Acquired for a research image collection, with no referral diagnosis. Dermoscopy of a skin lesion. The patient says their skin tans without first burning. Few moles overall by the patient's own estimate — 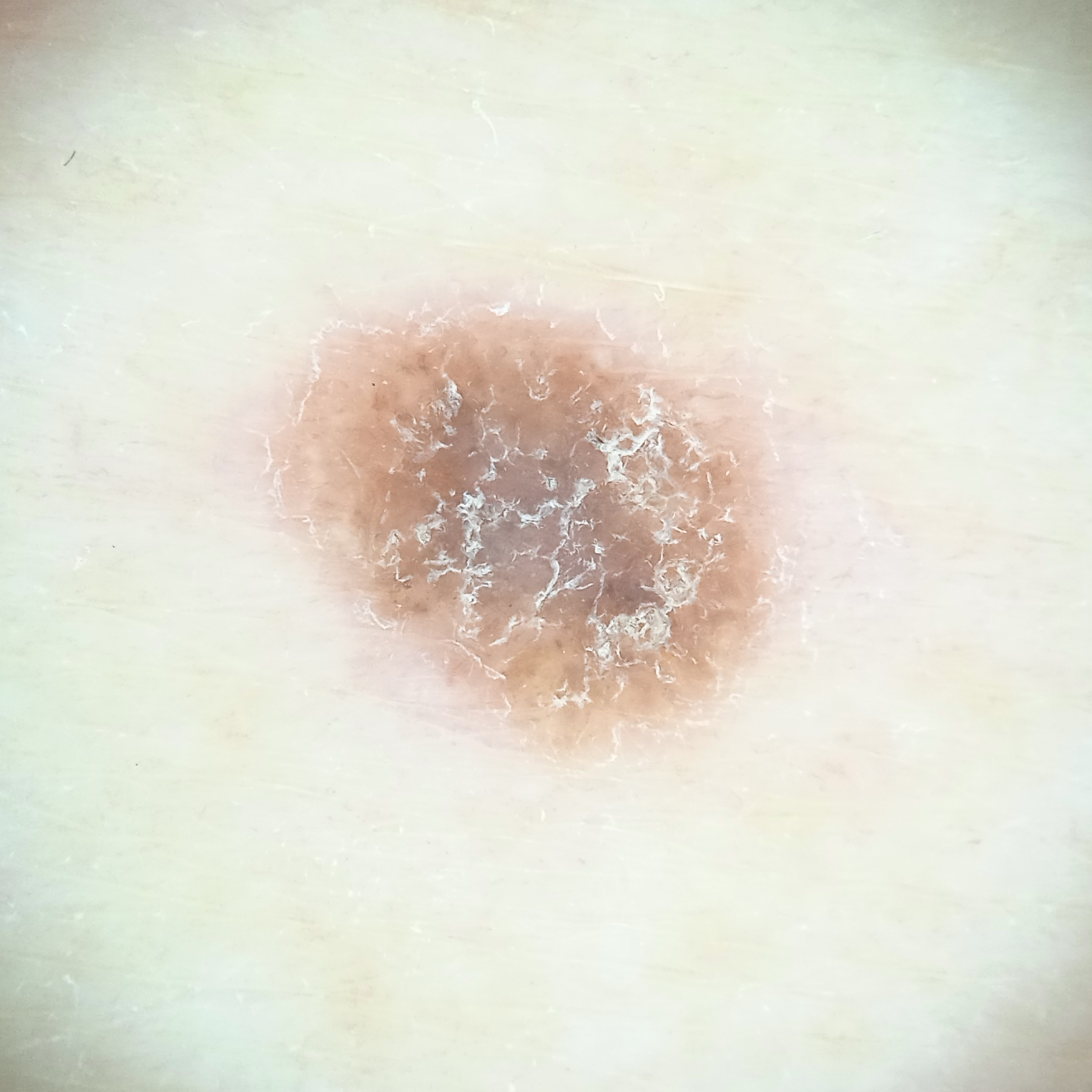The lesion measures approximately 5.9 mm. Dermatologist review favored a seborrheic keratosis.